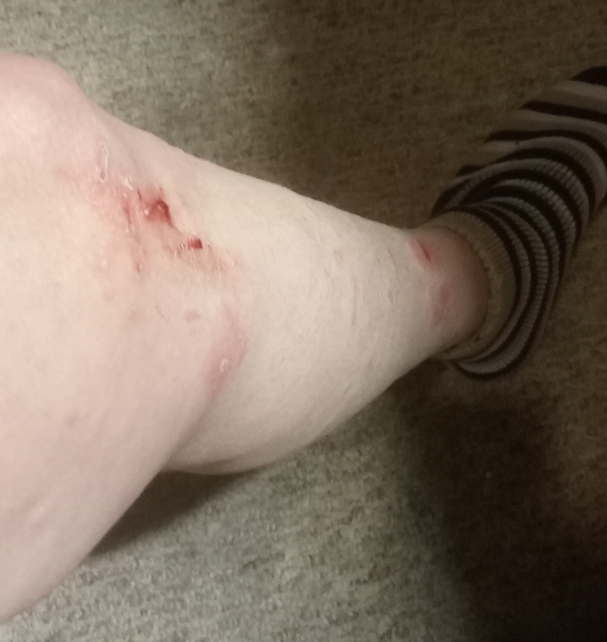Q: Reported symptoms?
A: pain, burning, bleeding, itching, darkening and enlargement
Q: How was the photo taken?
A: at a distance
Q: What is the patient's skin tone?
A: self-reported FST III
Q: What is the affected area?
A: head or neck, arm, back of the hand, back of the torso and leg
Q: Any systemic symptoms?
A: chills, fatigue and joint pain
Q: Patient's own categorization?
A: skin that appeared healthy to them
Q: Duration?
A: one to four weeks
Q: Texture?
A: rough or flaky, raised or bumpy, flat and fluid-filled
Q: Who is the patient?
A: female, age 40–49
Q: What is the differential diagnosis?
A: the impression on review was Allergic Contact Dermatitis